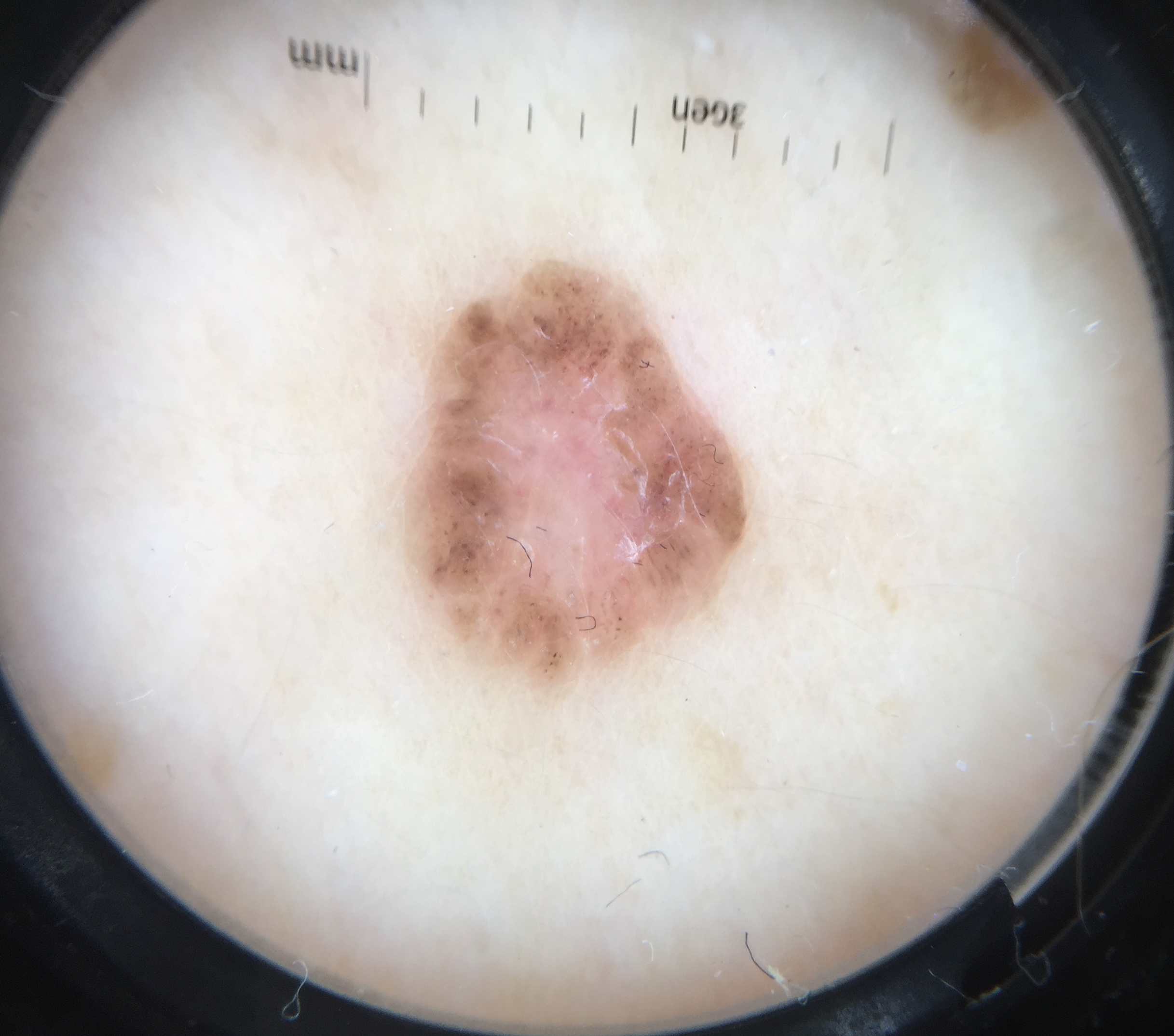• modality: dermatoscopy
• lesion type: keratinocytic
• pathology: basal cell carcinoma (biopsy-proven)